A dermoscopy image of a skin lesion. A male patient 77 years of age. The patient says their skin reddens with sun exposure. On a questionnaire the patient reported a personal history of cancer, a personal history of skin cancer, no prior organ transplant, and no family history of skin cancer — 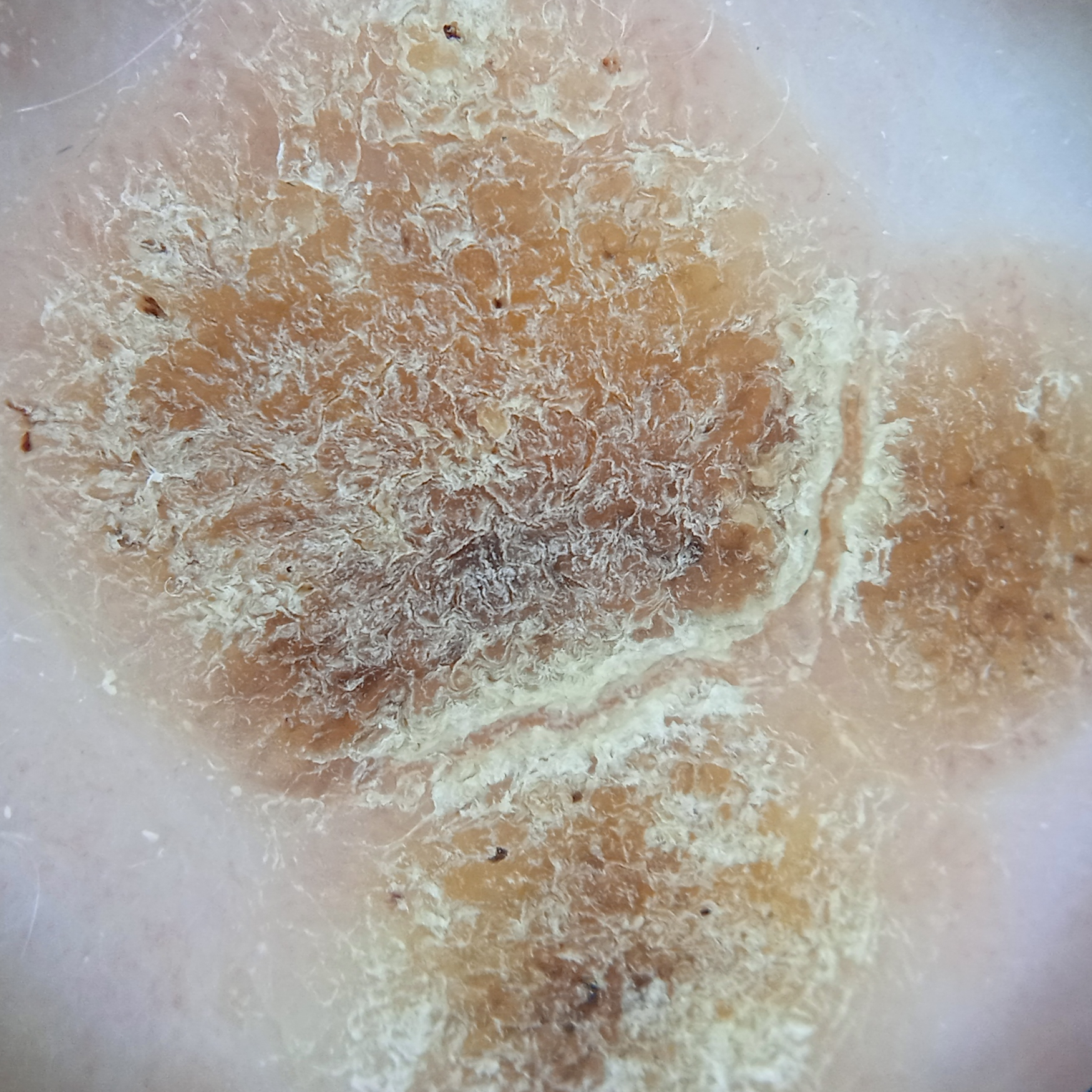The lesion involves the back. Measuring roughly 14.2 mm. The dermatologists' assessment was a seborrheic keratosis.